The lesion is associated with bothersome appearance, enlargement and darkening · the lesion is described as raised or bumpy · the patient indicates the condition has been present for one to three months · the patient reported no systemic symptoms · the lesion involves the leg · the patient considered this a rash · female contributor, age 18–29 · this is a close-up image — 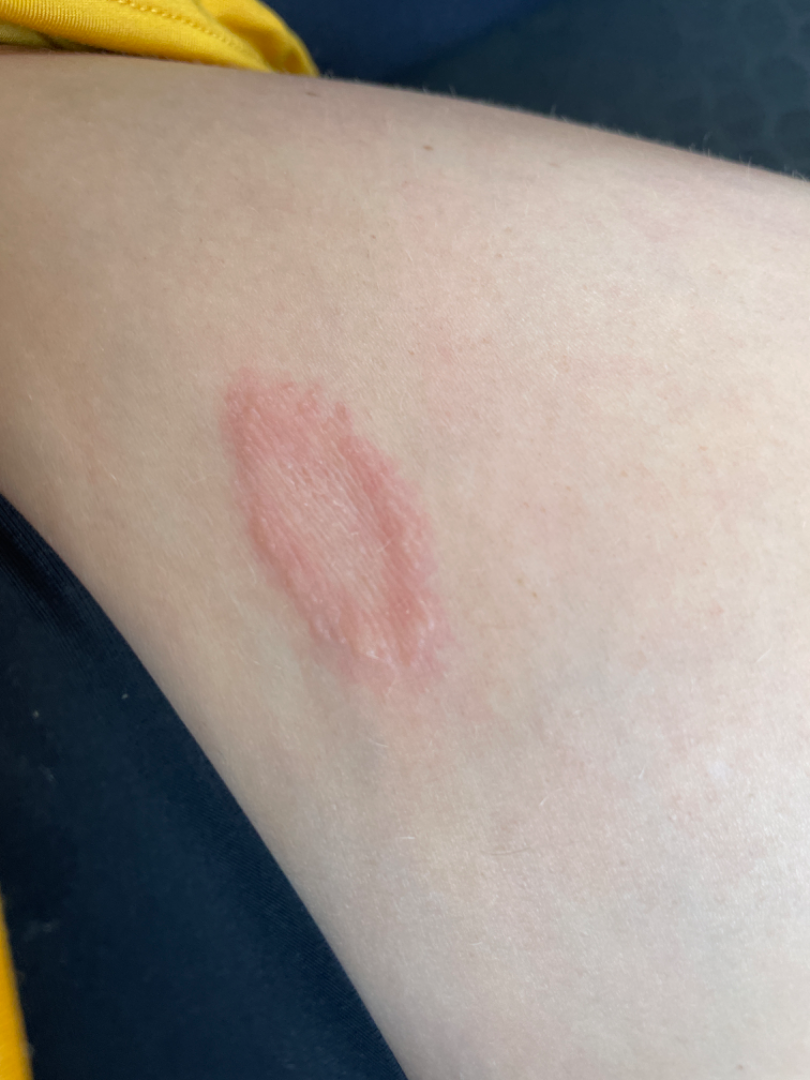dermatologist impression: Pityriasis rosea and Erythema annulare centrifugum were considered with similar weight; lower on the differential is Eczema; less probable is Tinea; a remote consideration is Psoriasis; less likely is Granuloma annulare.